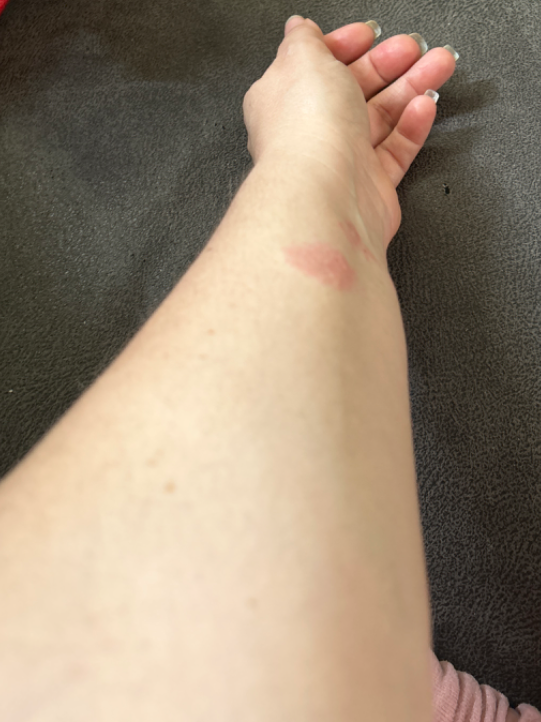subject: female, age 40–49 | shot type: at an angle | affected area: arm | dermatologist impression: consistent with Allergic Contact Dermatitis.